A close-up photograph · the contributor is 18–29, male · the back of the torso is involved: 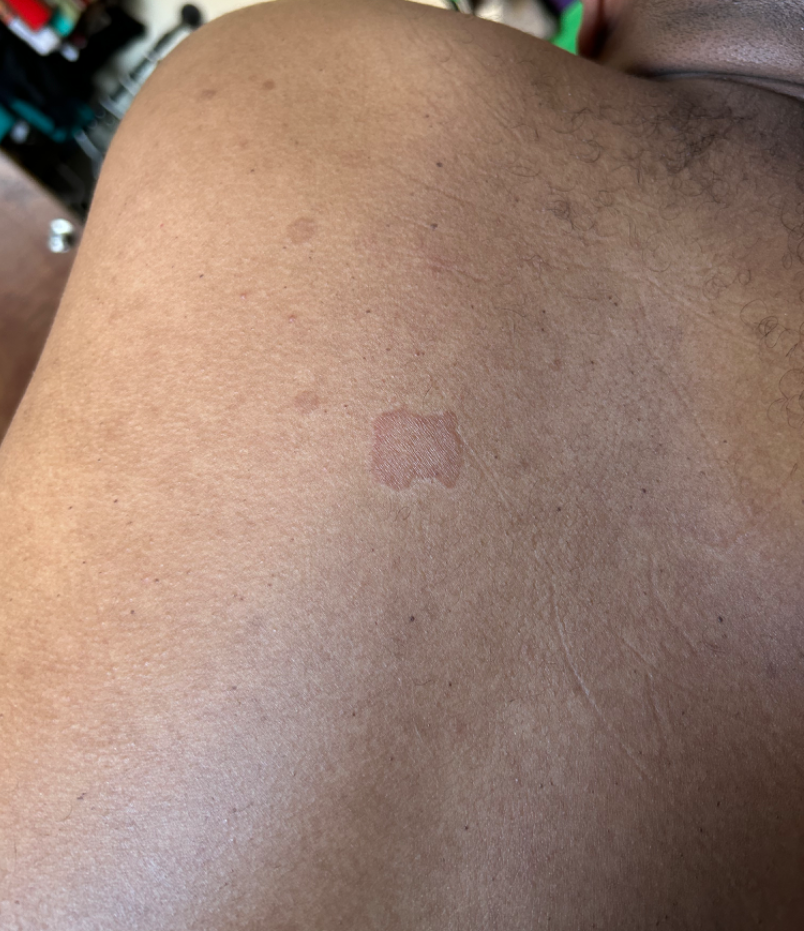Case summary:
• patient-reported symptoms: none reported
• present for: about one day
• associated systemic symptoms: none reported
• surface texture: raised or bumpy
• clinical impression: Actinic Keratosis (possible); SCC/SCCIS (possible); Basal Cell Carcinoma (remote)